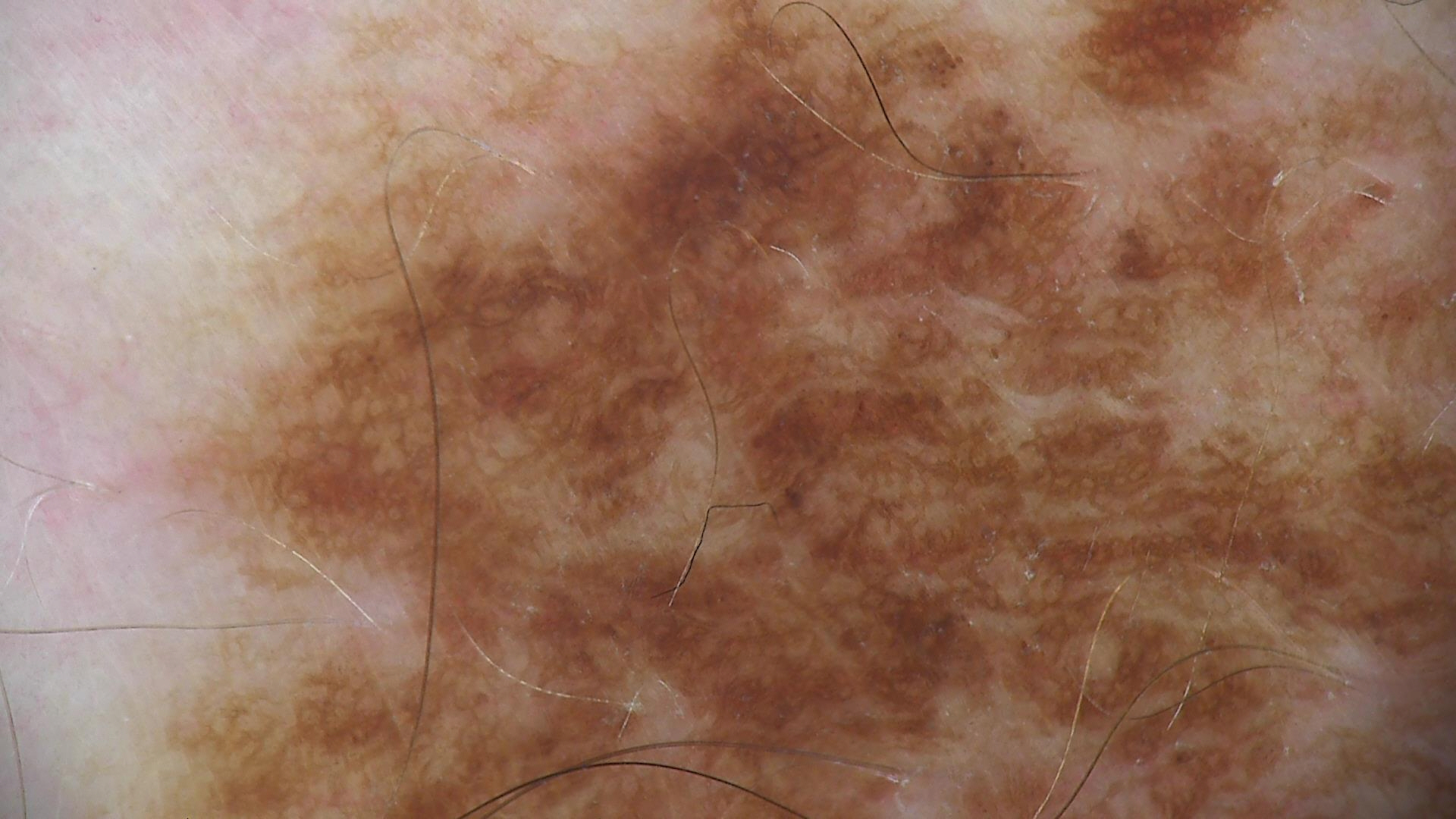A skin lesion imaged with a dermatoscope.
The architecture is that of a banal lesion.
The diagnosis was a congenital junctional nevus.